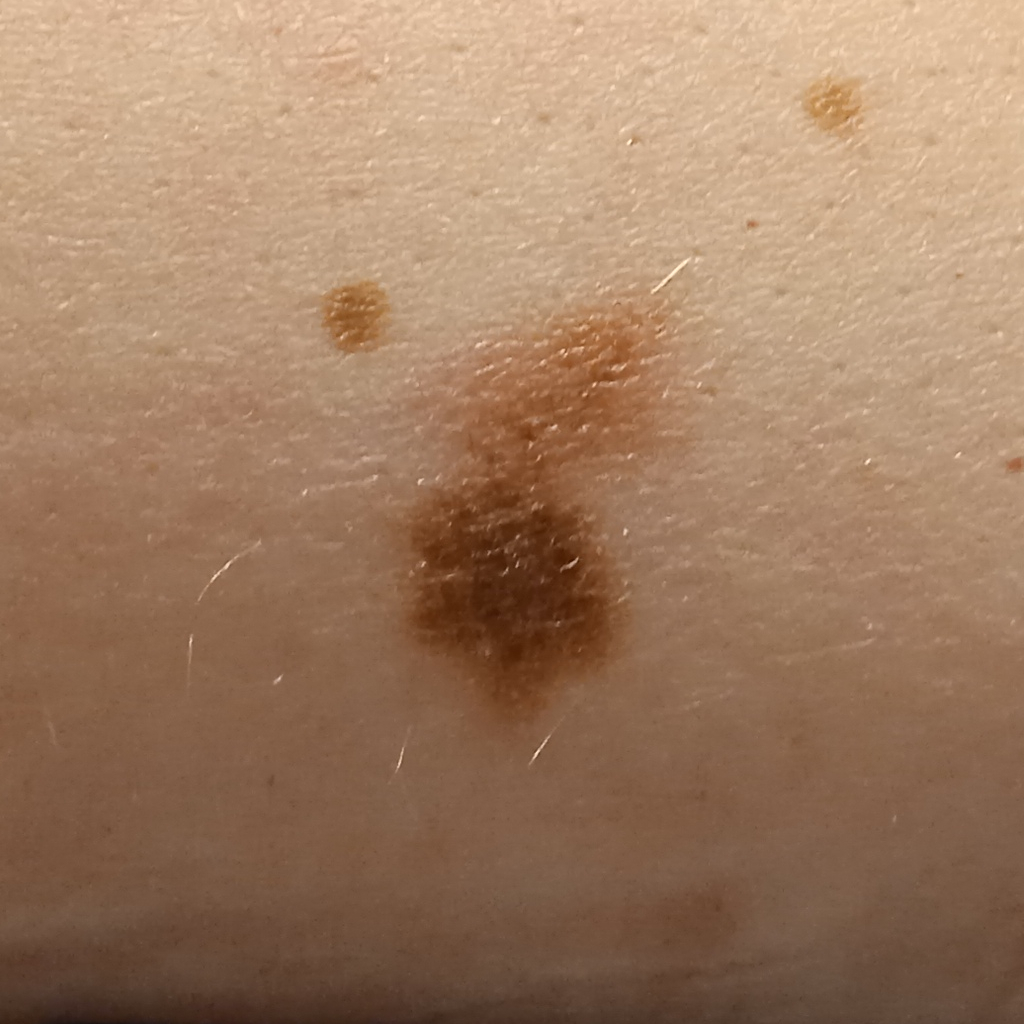By self-report, a personal history of cancer, a family history of skin cancer, and a personal history of skin cancer. The patient describes having numerous moles. Acquired for a research image collection, with no referral diagnosis. A clinical close-up of a skin lesion. The patient says their skin reddens with sun exposure. The lesion is on the torso. Measuring roughly 17.5 mm. The diagnostic impression was a melanoma.